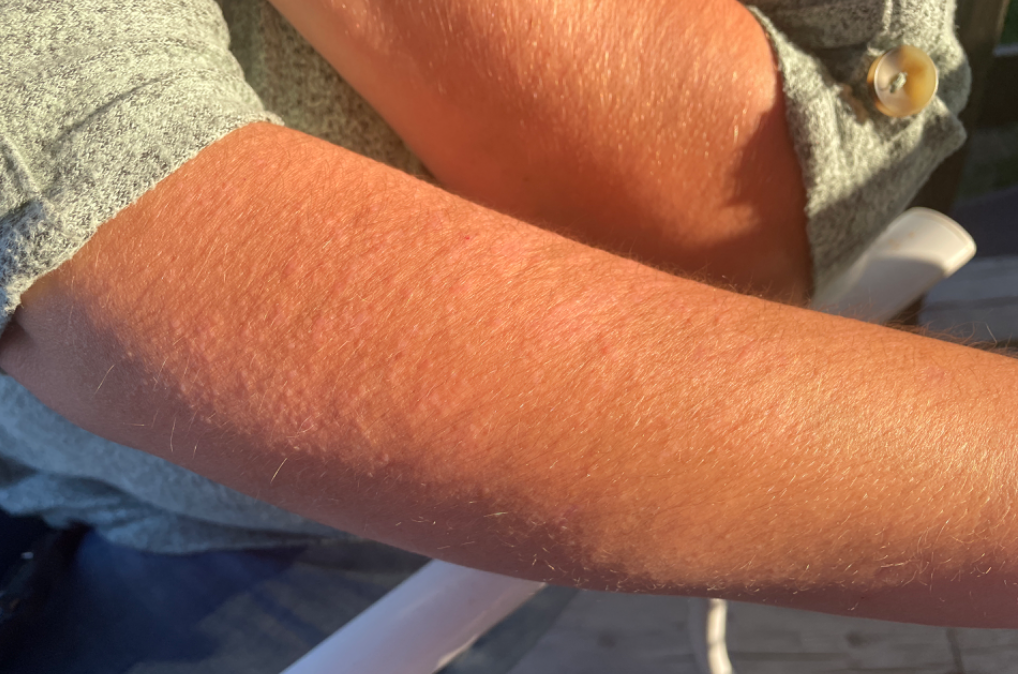Case summary:
• assessment: indeterminate
• affected area: arm and head or neck
• image framing: at an angle
• contributor: female, age 30–39